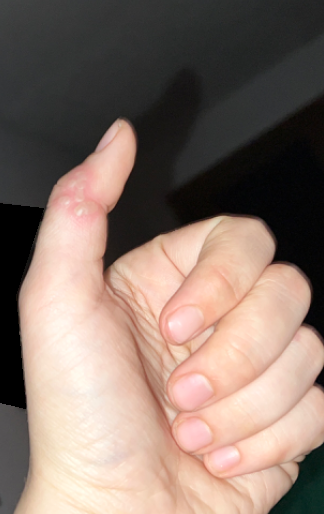The subject is a female aged 18–29.
The patient notes the lesion is fluid-filled.
No relevant systemic symptoms.
The patient notes pain.
Reported duration is less than one week.
This image was taken at a distance.
Skin tone: Fitzpatrick phototype III; human graders estimated a Monk skin tone scale of 2.
Self-categorized by the patient as a rash.
A single dermatologist reviewed the case: consistent with Herpes Simplex.